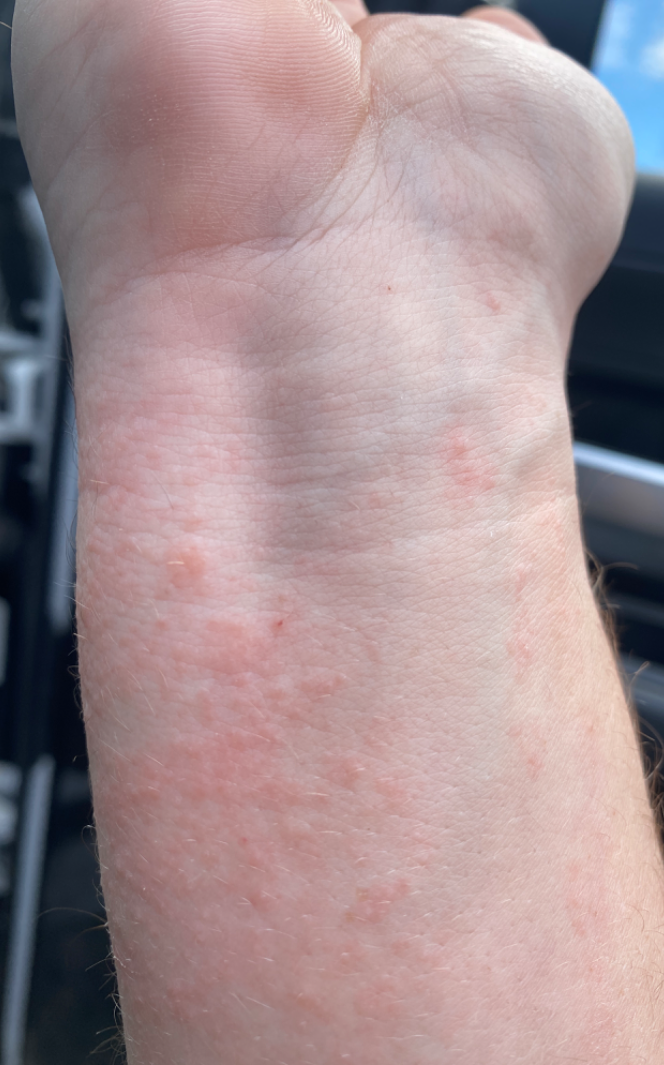Patient information: The condition has been present for less than one week. Located on the arm. Reported lesion symptoms include itching and bothersome appearance. Skin tone: non-clinician graders estimated Monk Skin Tone 2. The patient notes the lesion is raised or bumpy. Self-categorized by the patient as a rash. A close-up photograph. Review: Acute dermatitis, NOS (100%).